A patient 60 years of age · a smartphone photograph of a skin lesion:
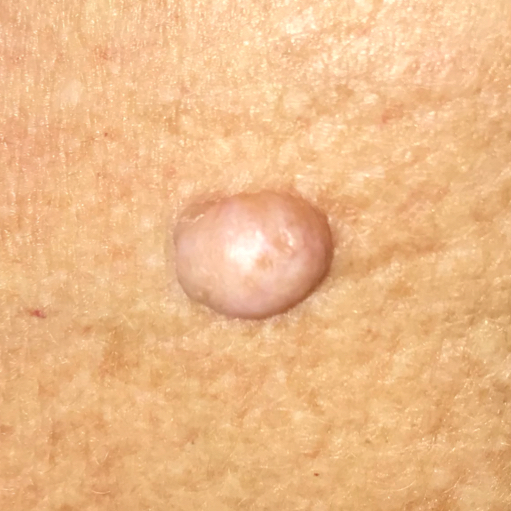Clinical context:
The lesion is on the chest.
Conclusion:
Clinically diagnosed as a nevus.